The affected area is the back of the hand. The patient is a female aged 18–29. The photograph was taken at a distance — 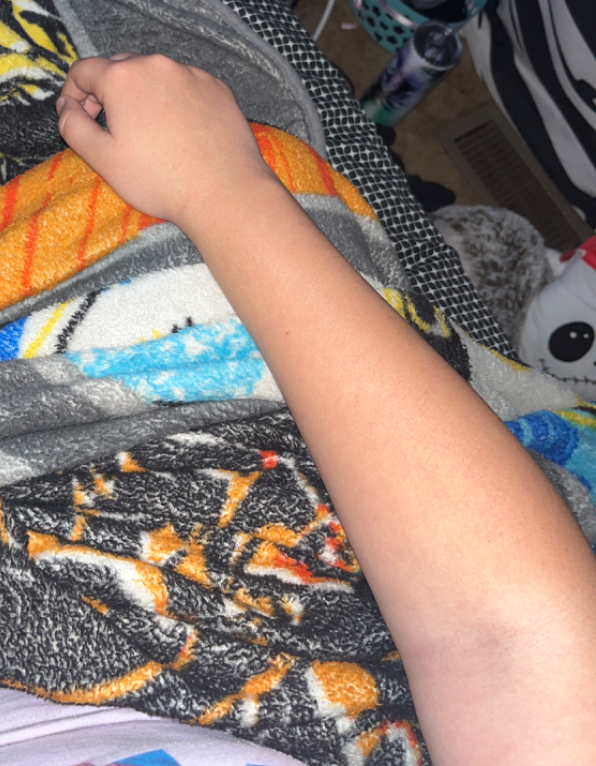Findings:
– assessment — could not be assessed
– self-categorized as — a rash
– texture — raised or bumpy
– patient-reported symptoms — itching